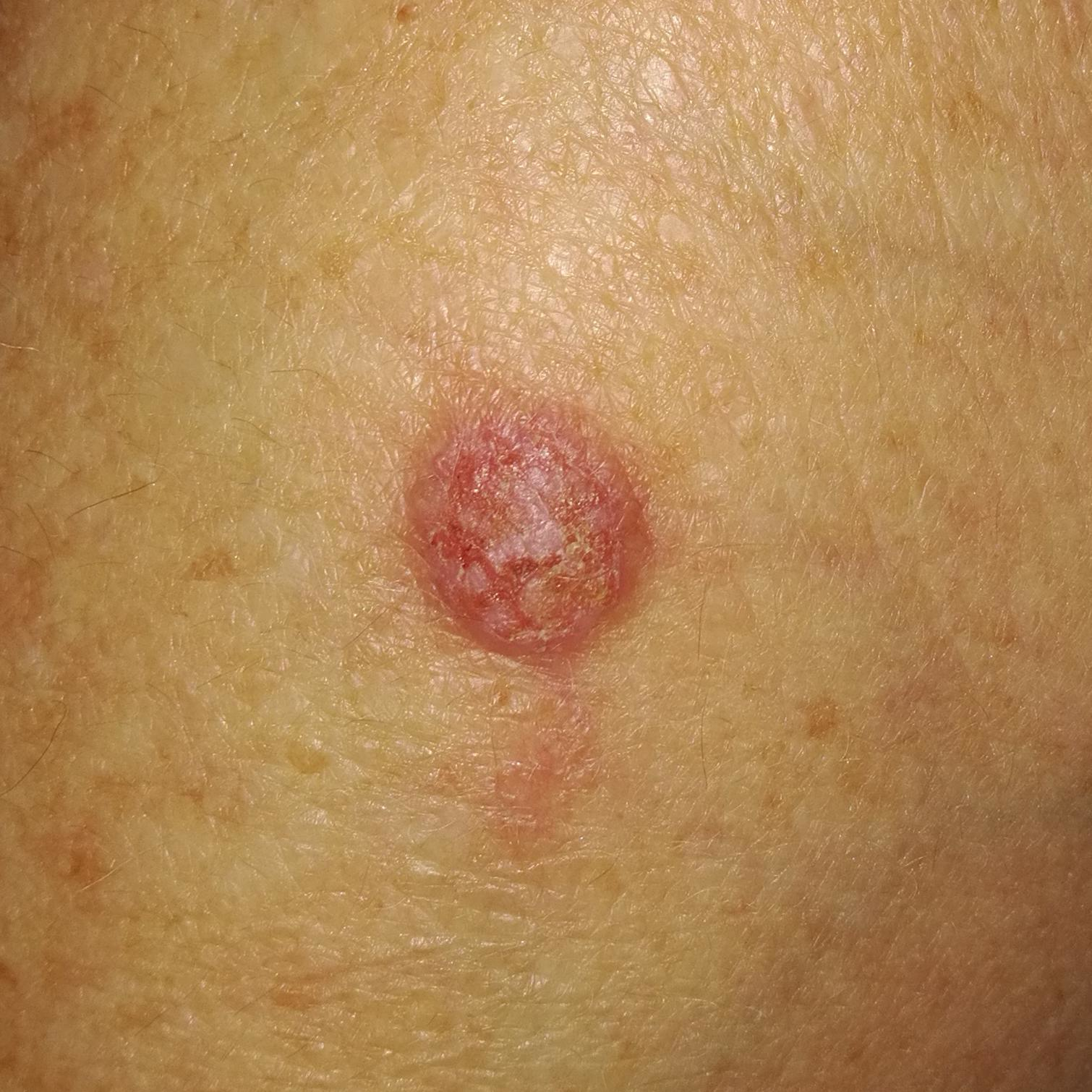  skin_type: I
  image: clinical photograph
  risk_factors:
    positive:
      - prior cancer (patient or family)
  patient:
    age: 83
    gender: male
  lesion_location: the chest
  lesion_size:
    diameter_1_mm: 15.0
    diameter_2_mm: 13.0
  symptoms:
    present:
      - itching
      - elevation
  diagnosis:
    name: squamous cell carcinoma
    code: SCC
    malignancy: malignant
    confirmation: histopathology